The subject is a male aged 40–49 · close-up view · self-categorized by the patient as a rash · the arm is involved · symptoms reported: itching and enlargement · no constitutional symptoms were reported · present for more than one year · the patient notes the lesion is rough or flaky.
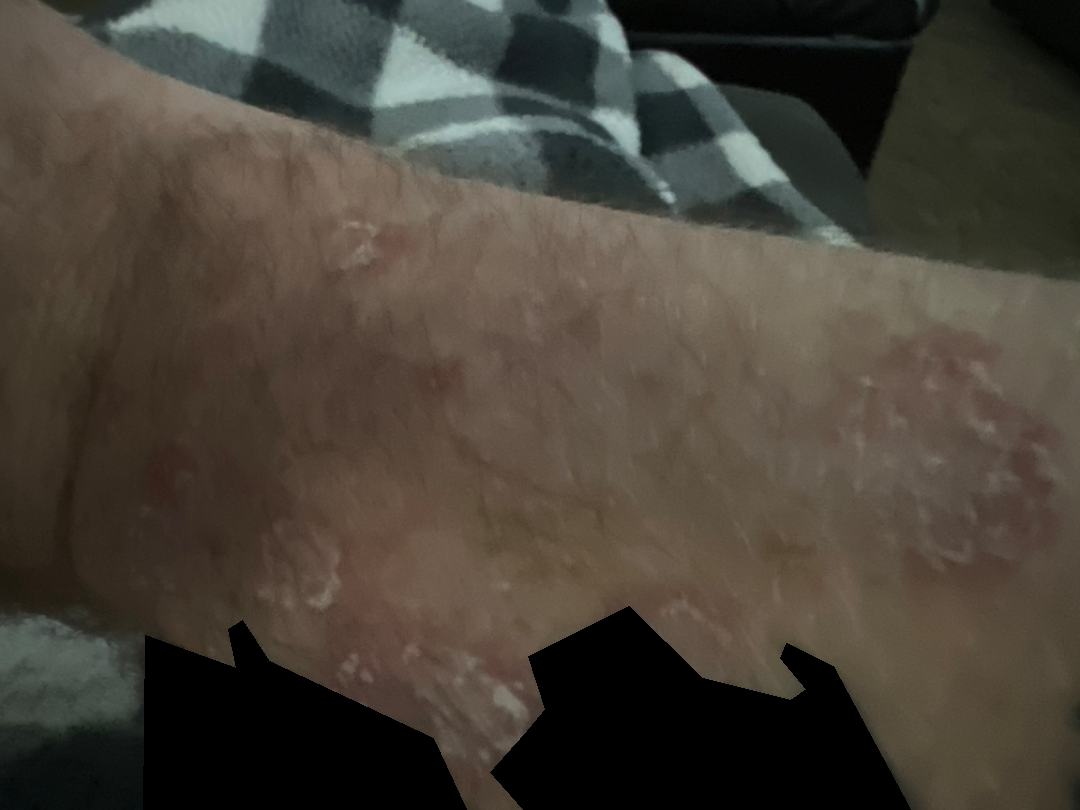Findings: The skin findings could not be characterized from the image.